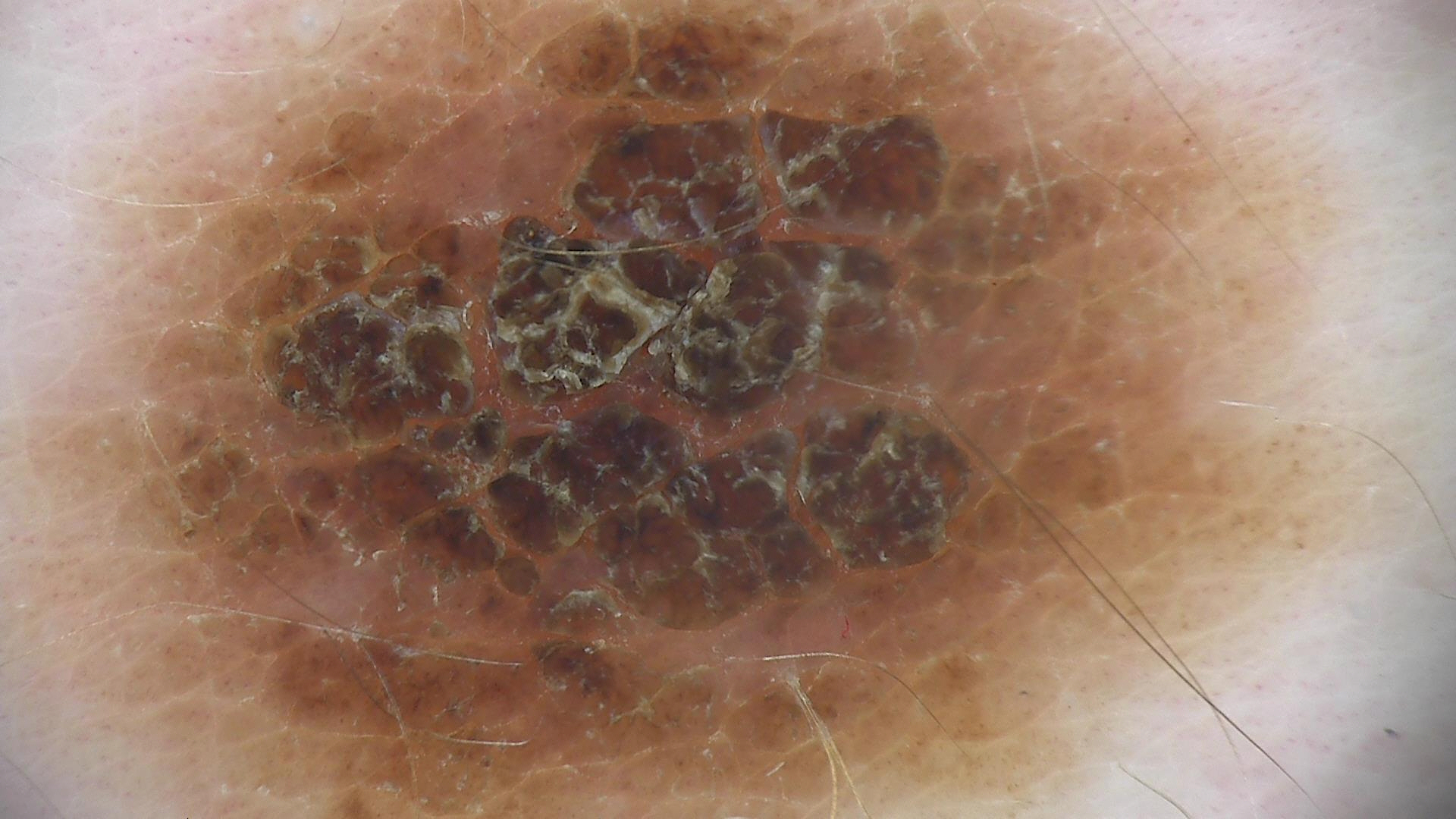image=dermoscopy
subtype=banal
label=congenital compound nevus (expert consensus)